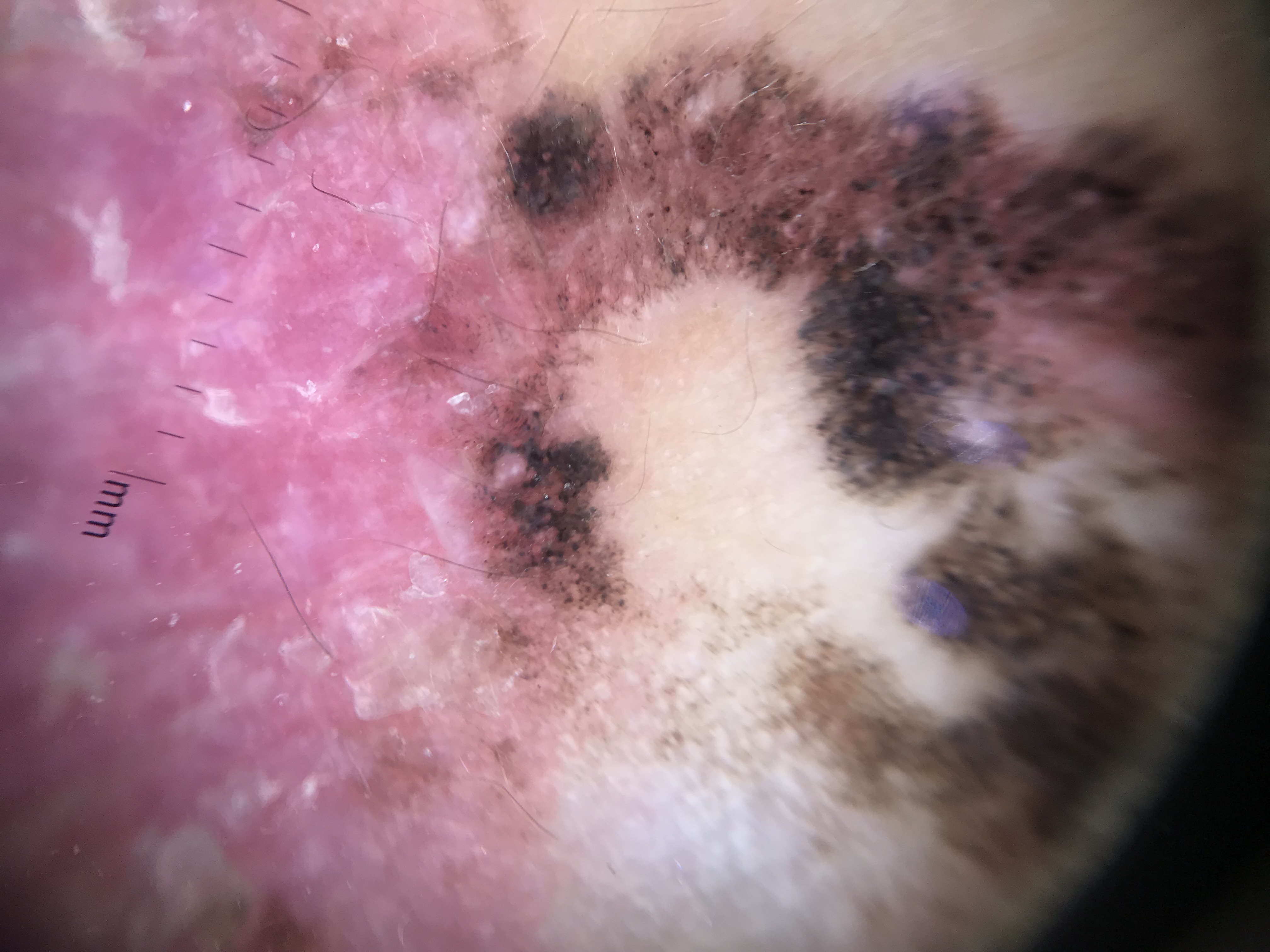Case: A skin lesion imaged with a dermatoscope. Diagnosis: Histopathology confirmed a malignancy — a melanoma.